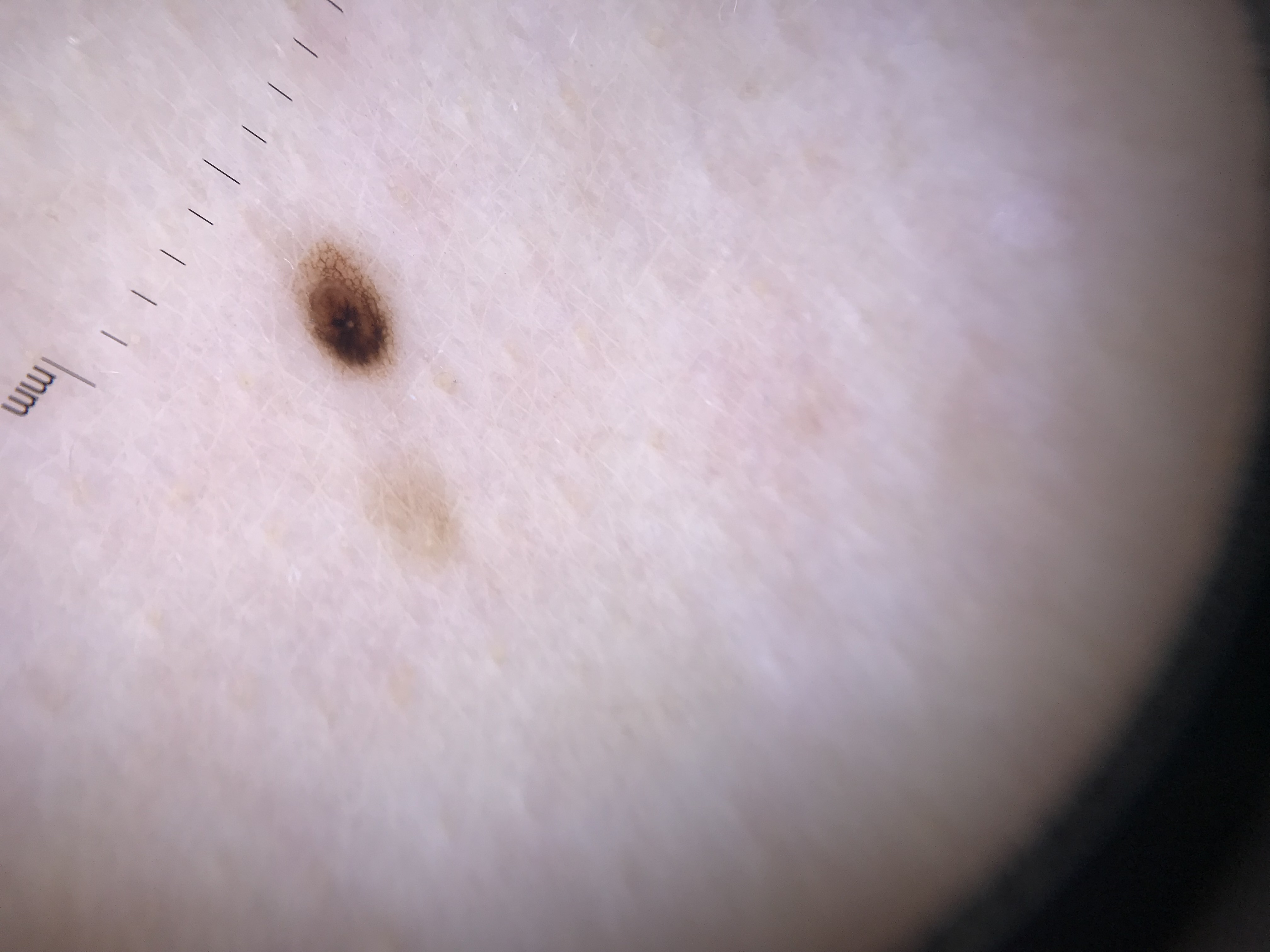| field | value |
|---|---|
| diagnosis | dysplastic compound nevus (expert consensus) |